A female subject aged around 70; contact-polarized dermoscopy of a skin lesion — 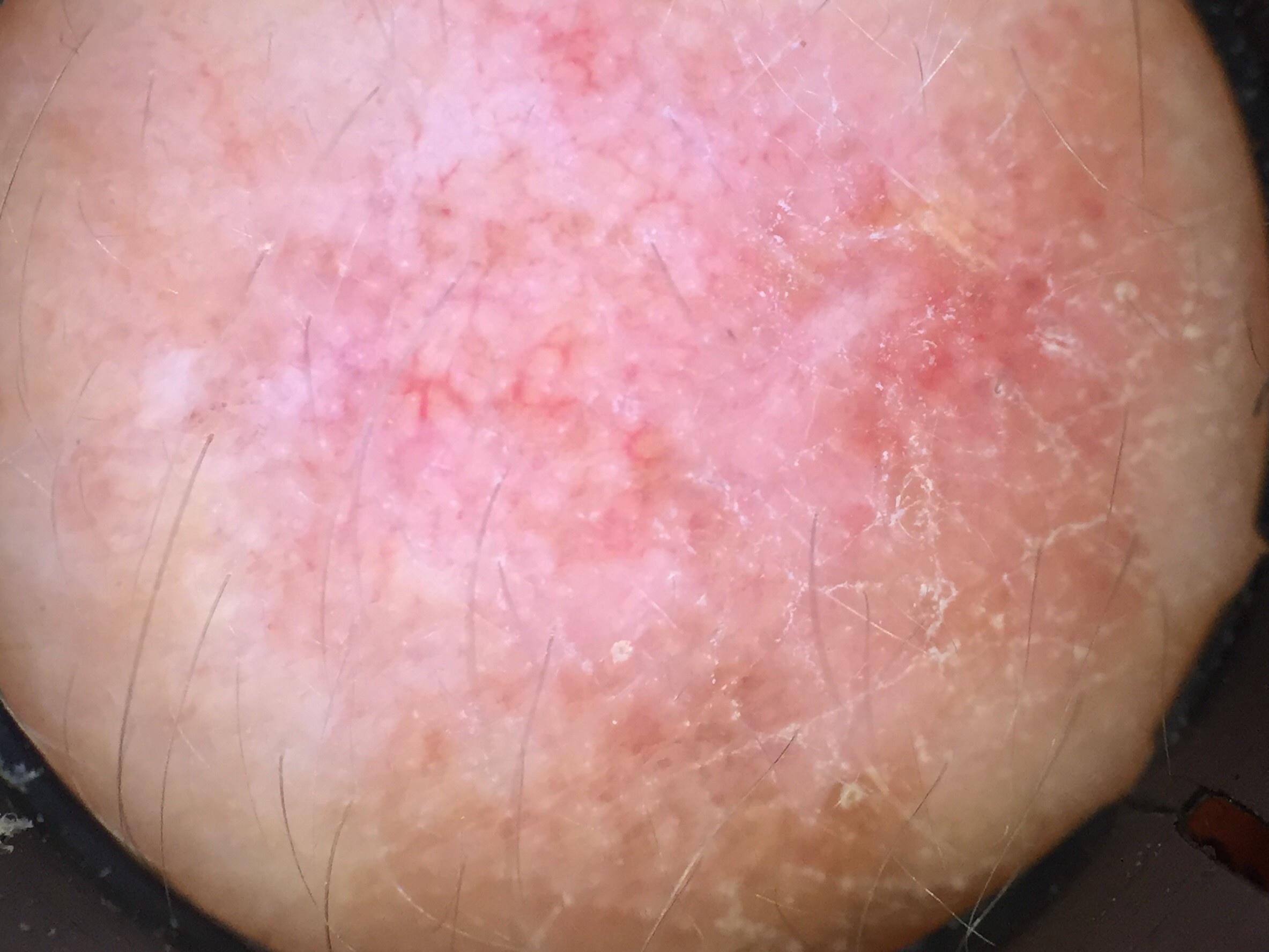site: the head or neck, diagnosis: Squamous cell carcinoma (biopsy-proven).